A dermoscopic image of a skin lesion · a female patient, aged around 25:
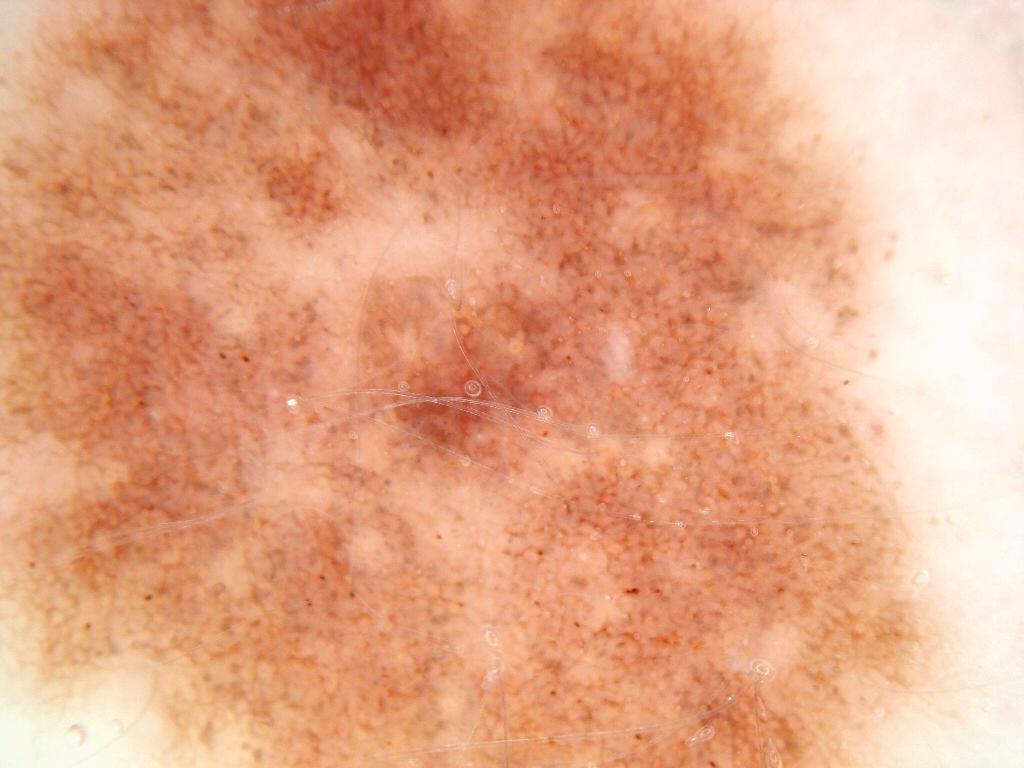dermoscopic pattern = pigment network, location = extends across the entire field of view, impression = a melanocytic nevus.